A skin lesion imaged with a dermatoscope: 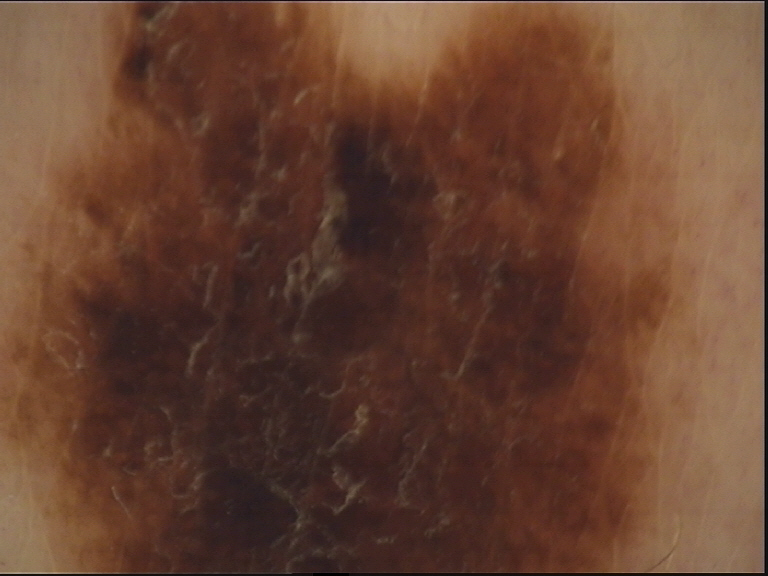Q: What was the diagnostic impression?
A: dysplastic compound nevus (expert consensus)